A dermoscopic photograph of a skin lesion:
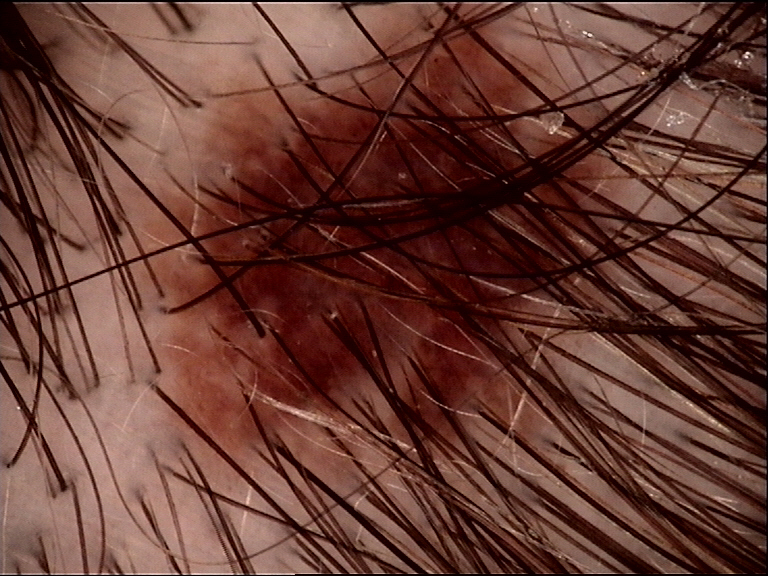The diagnosis was a dysplastic junctional nevus.